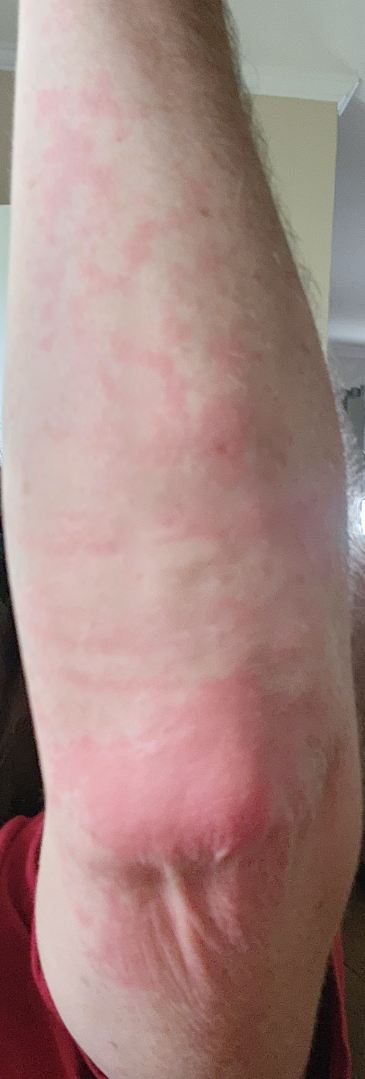Notes:
– assessment · unable to determine